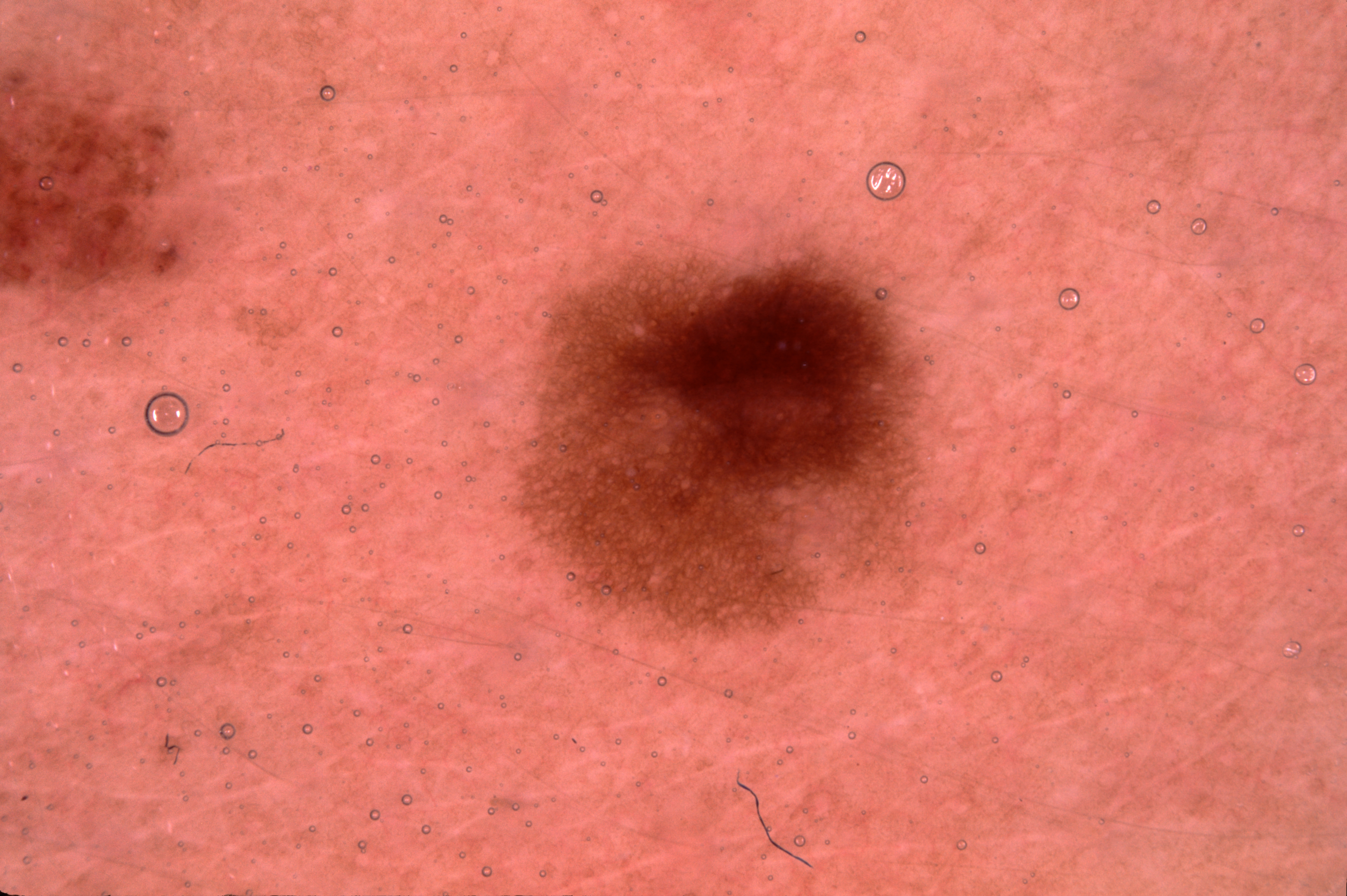A dermoscopic image of a skin lesion.
In (x1, y1, x2, y2) order, the lesion's extent is 503/211/954/649.
A mid-sized lesion within the field.
Dermoscopic review identifies pigment network.
The clinical diagnosis was a melanocytic nevus.